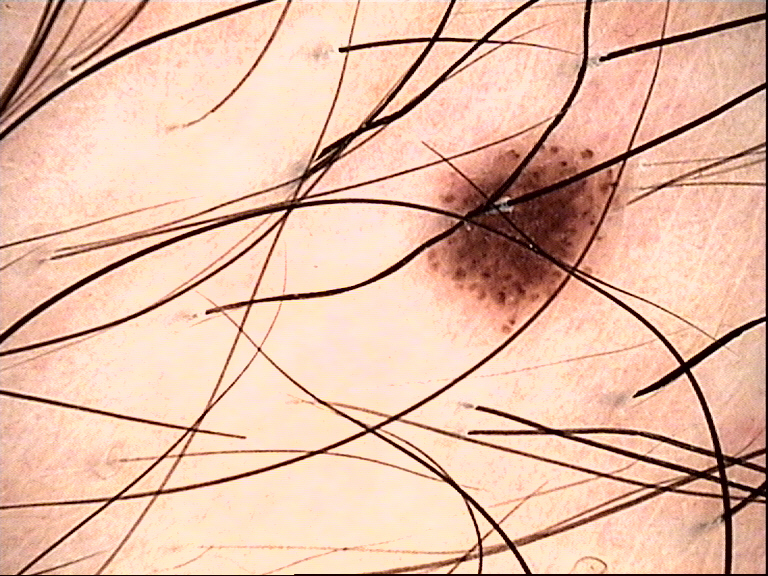{
  "diagnosis": {
    "name": "dysplastic junctional nevus",
    "code": "jd",
    "malignancy": "benign",
    "super_class": "melanocytic",
    "confirmation": "expert consensus"
  }
}